The photograph is a close-up of the affected area · the lesion involves the leg, head or neck and top or side of the foot — 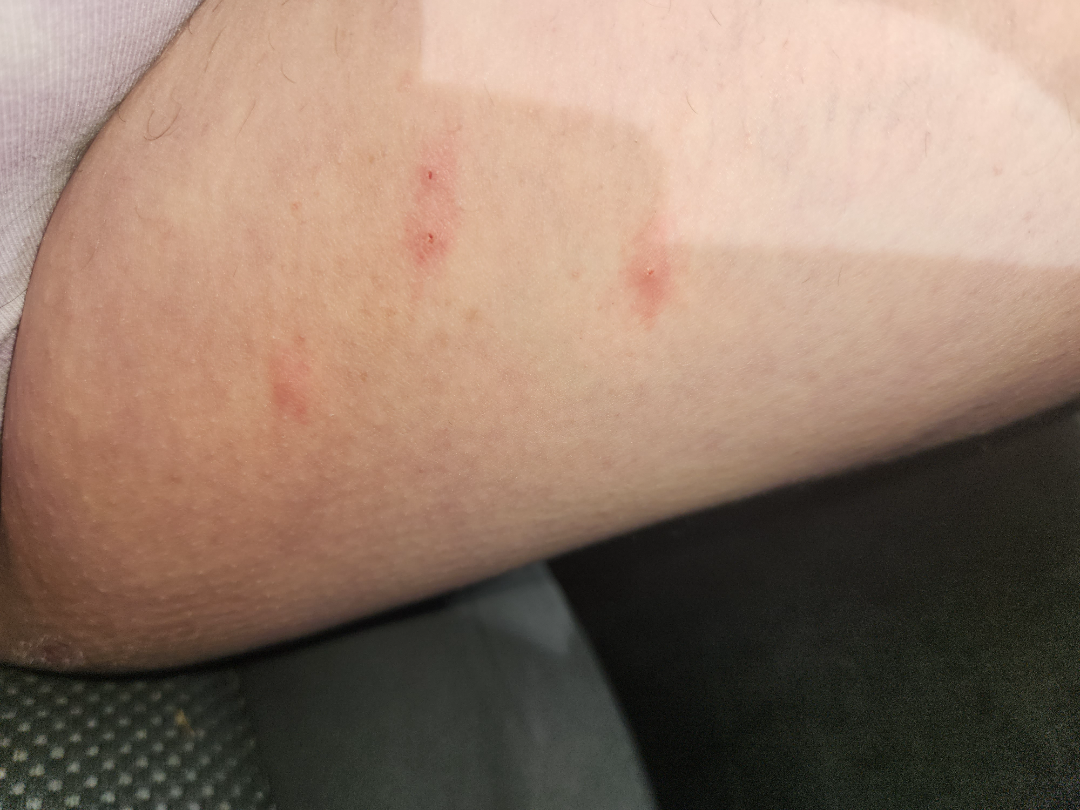The reviewer was unable to grade this case for skin condition. The patient described the issue as a rash. Texture is reported as fluid-filled and raised or bumpy. No constitutional symptoms were reported. Present for less than one week.